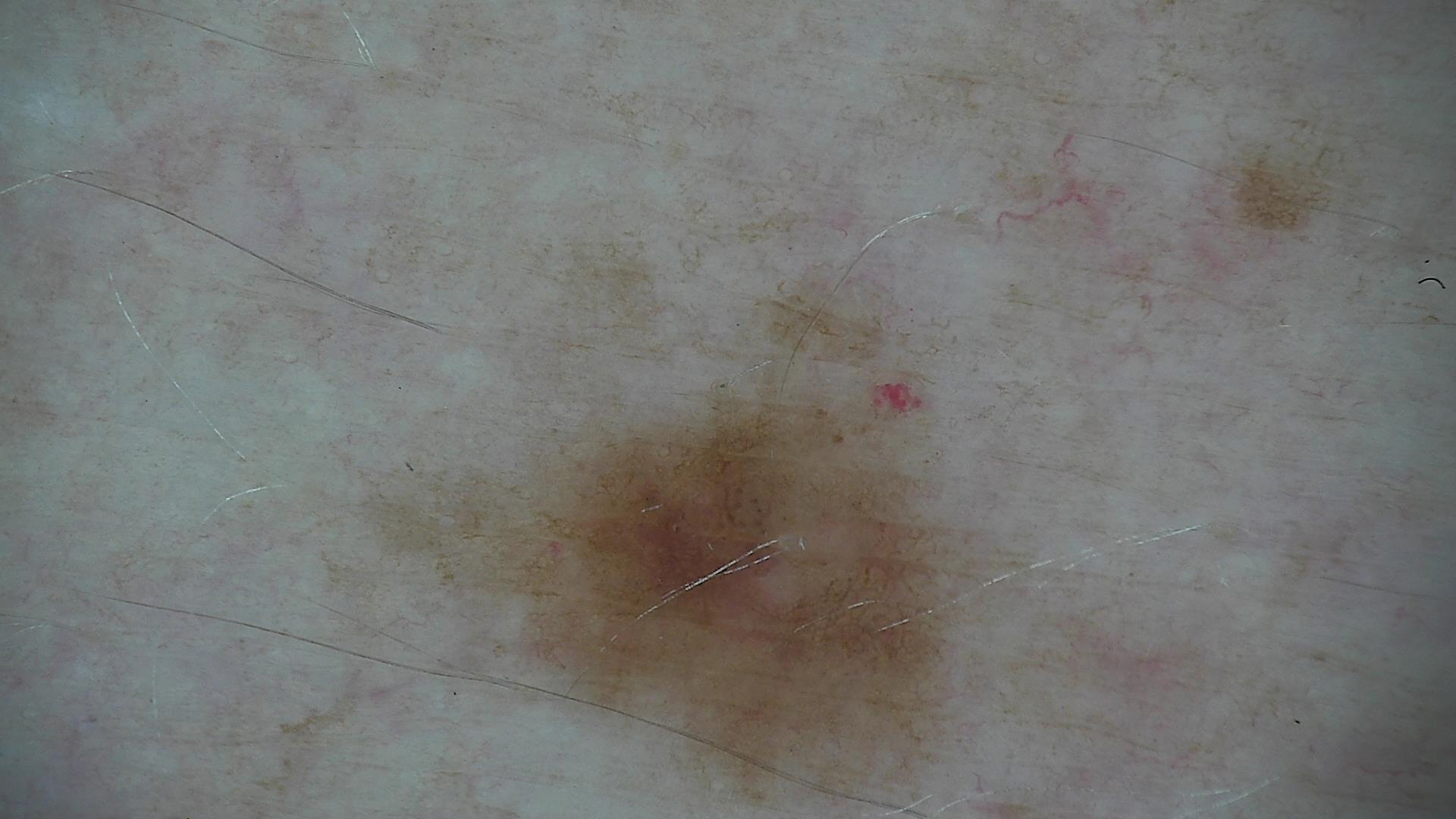Diagnosed as a dysplastic junctional nevus.